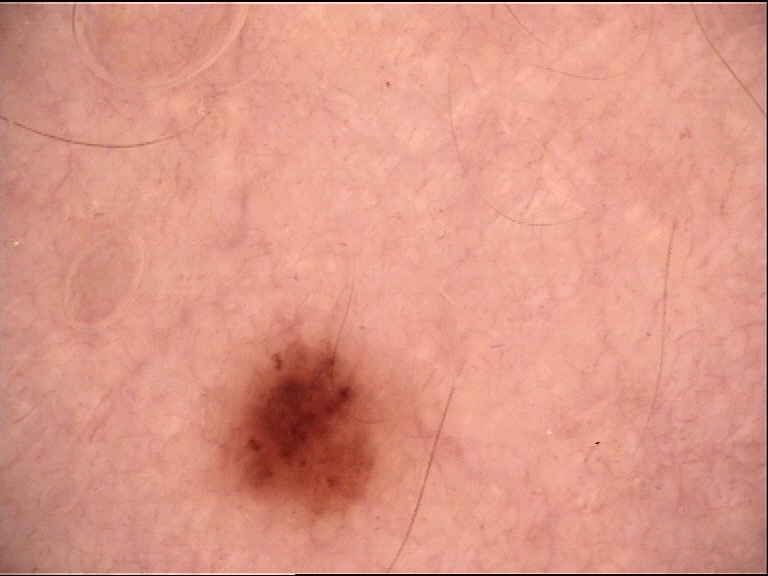Case:
– image · dermatoscopy
– class · dysplastic junctional nevus (expert consensus)